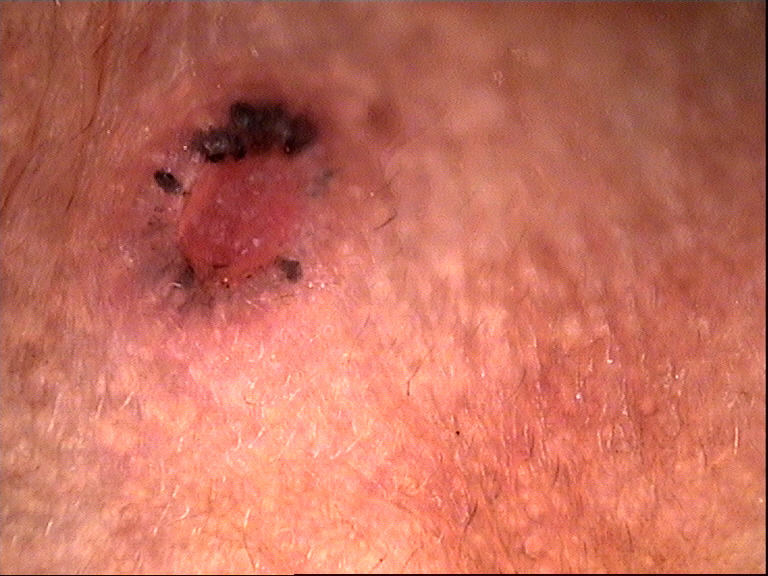A dermatoscopic image of a skin lesion. The morphology is that of a keratinocytic lesion. The biopsy diagnosis was a basal cell carcinoma.